The front of the torso is involved · the patient reports pain and itching · this is a close-up image · reported duration is less than one week · the subject is a female aged 18–29 · the patient reported no systemic symptoms · the lesion is described as fluid-filled and raised or bumpy · the patient described the issue as a rash:
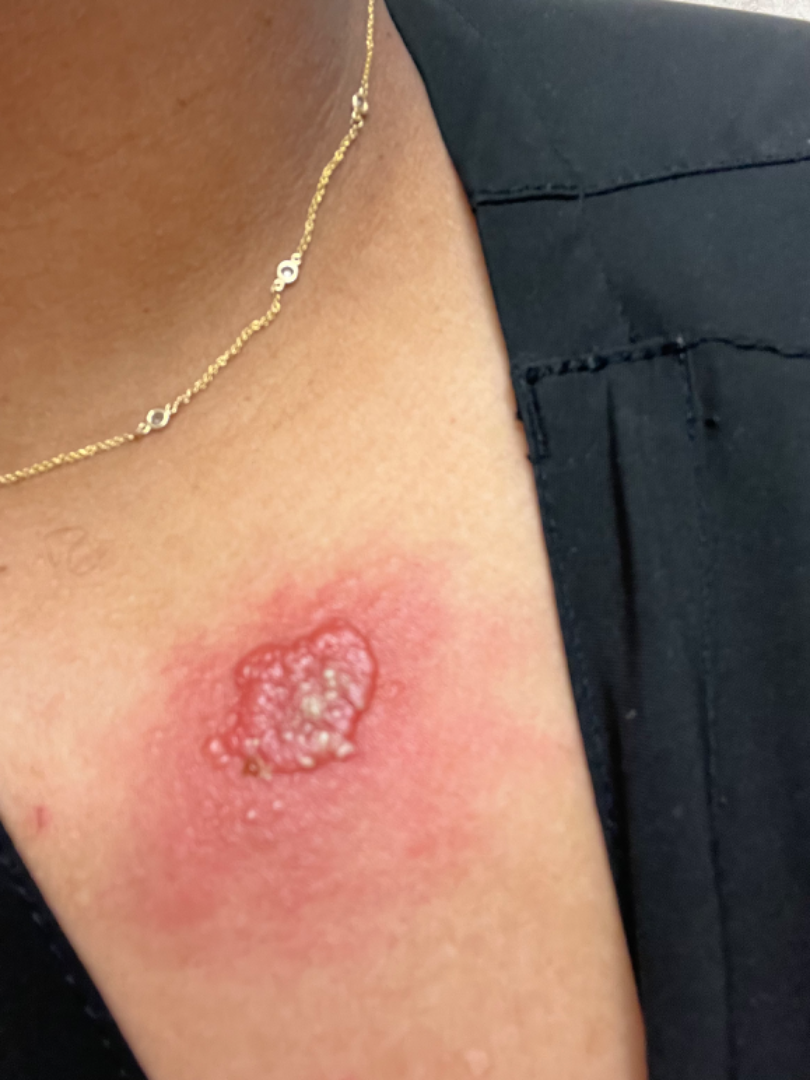{
  "differential": {
    "tied_lead": [
      "Impetigo",
      "Herpes Zoster"
    ]
  }
}